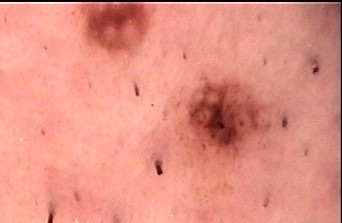Conclusion: The diagnostic label was a Miescher nevus.